A dermoscopy image of a single skin lesion:
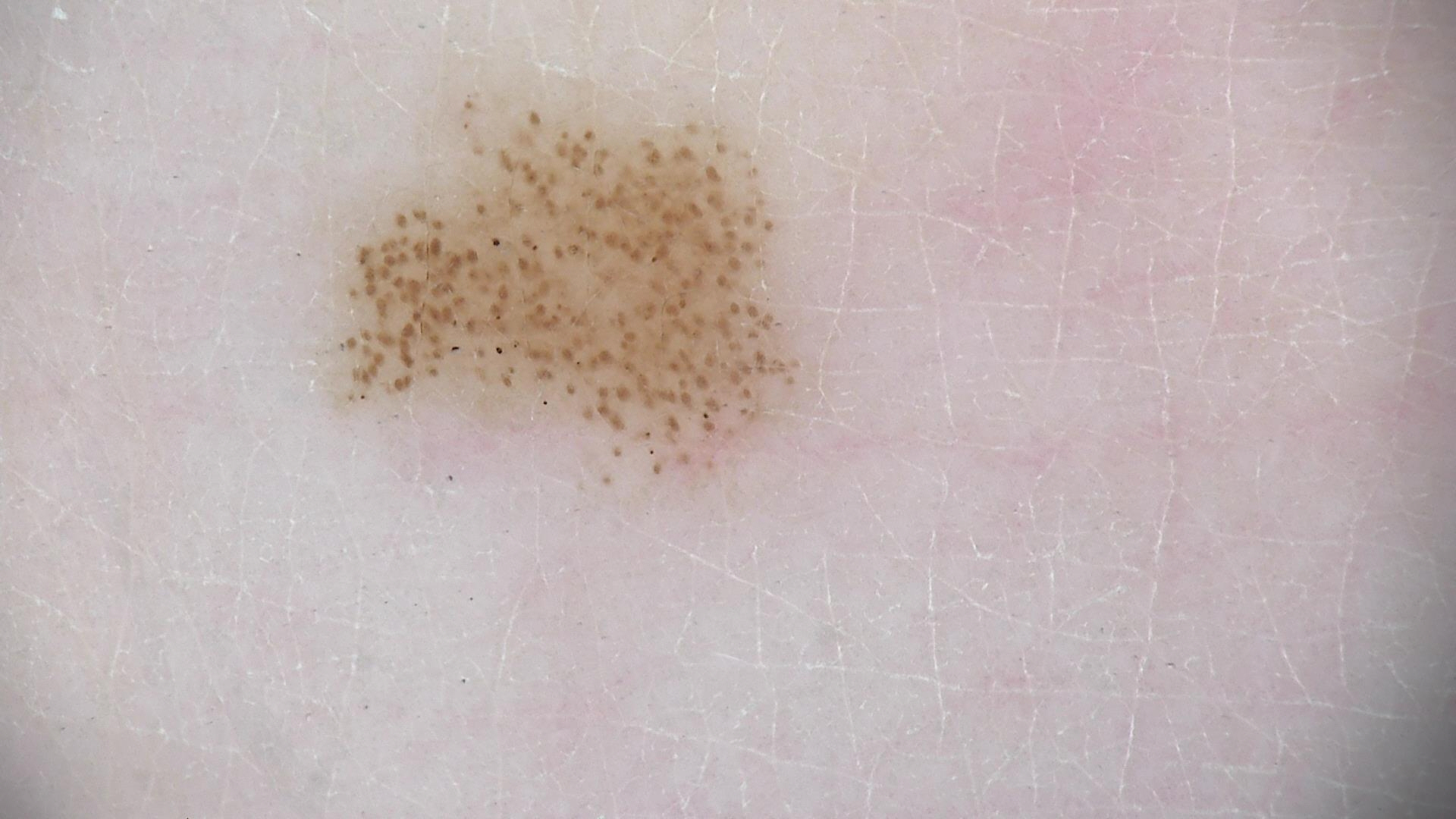The diagnostic label was a dysplastic junctional nevus.